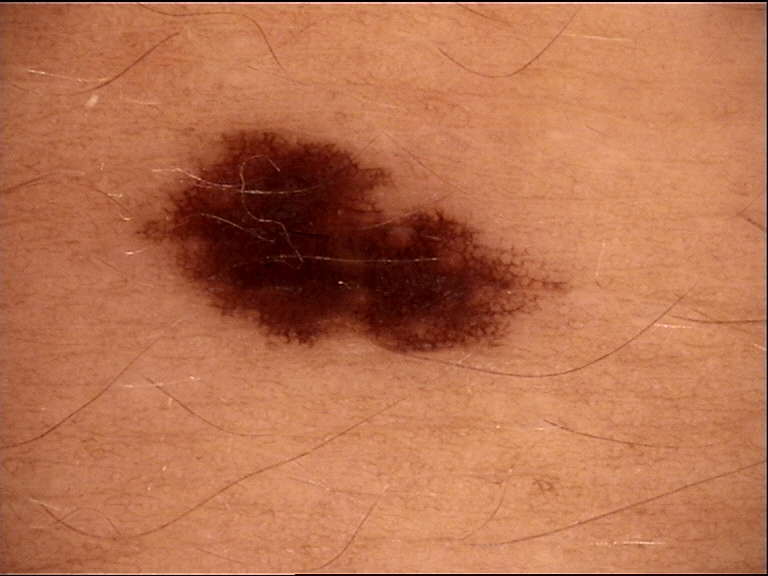Findings:
* imaging: dermatoscopy
* subtype: banal
* assessment: junctional nevus (expert consensus)